Symptoms reported: bothersome appearance, enlargement and itching. Lay graders estimated Monk skin tone scale 1 or 2. The photo was captured at a distance. The arm and back of the hand are involved. No relevant systemic symptoms. The patient considered this a rash: 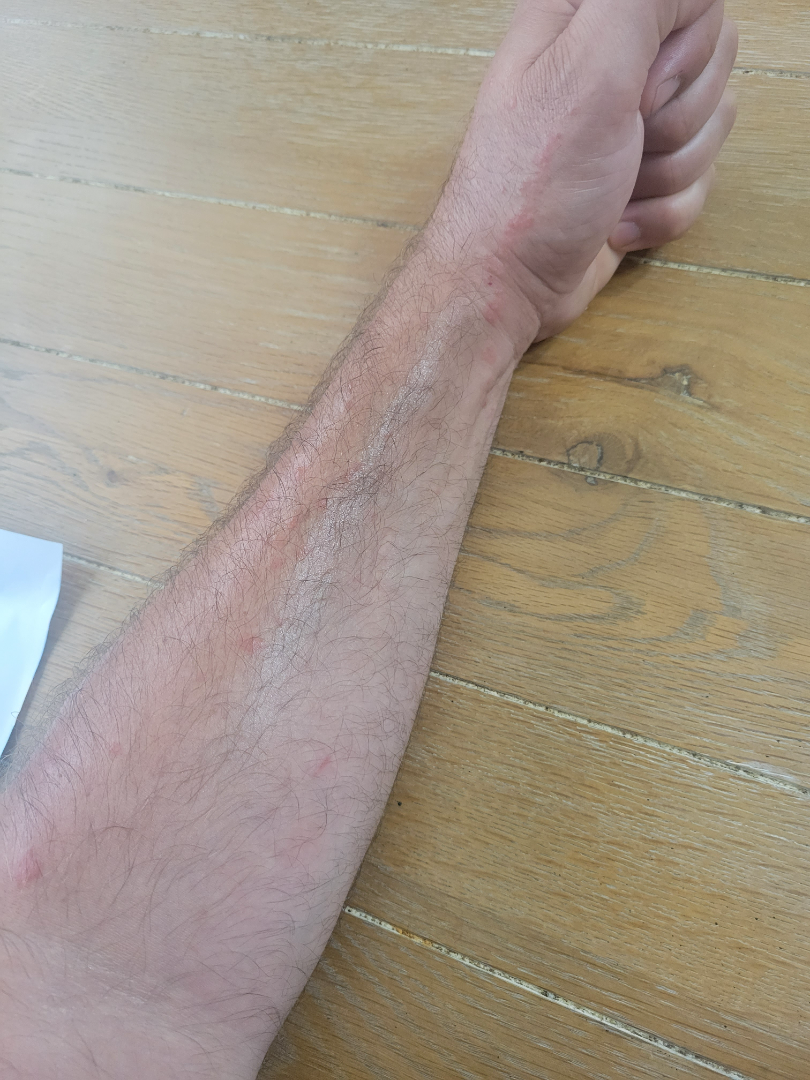{"assessment": "ungradable on photographic review"}